This is a dermoscopic photograph of a skin lesion: 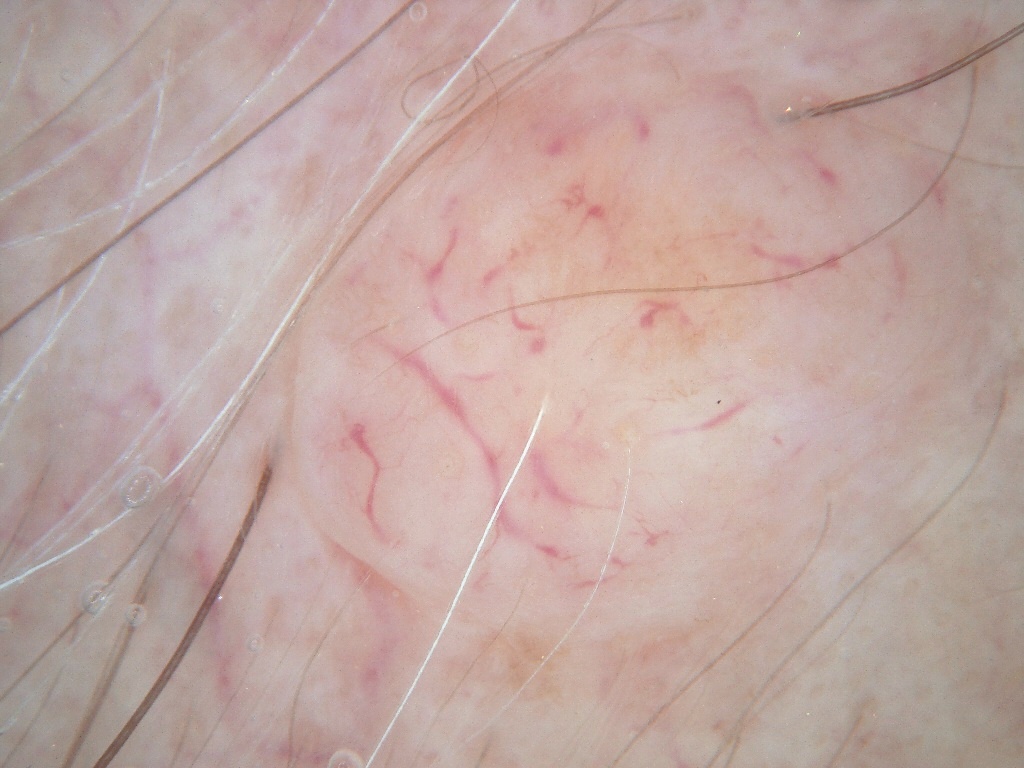Summary:
As (left, top, right, bottom), the lesion is located at 288 20 986 653.
Assessment:
Clinically diagnosed as a melanocytic nevus.